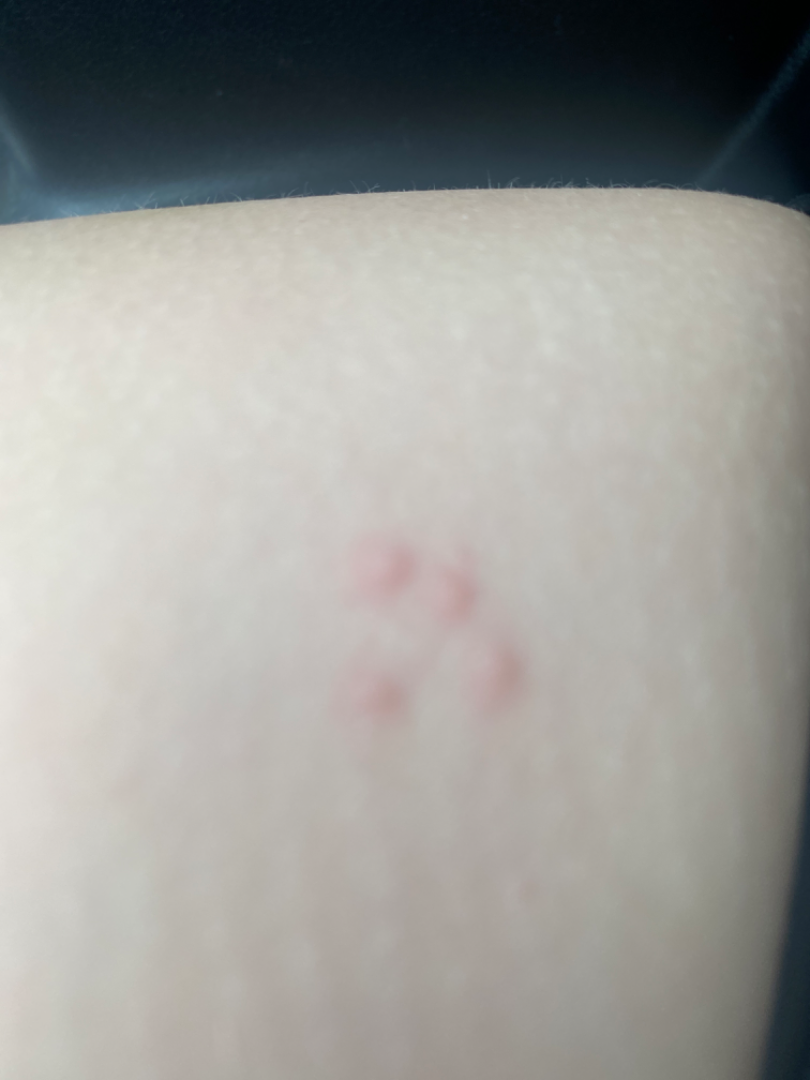No differential diagnosis could be assigned on photographic review.
This is a close-up image.